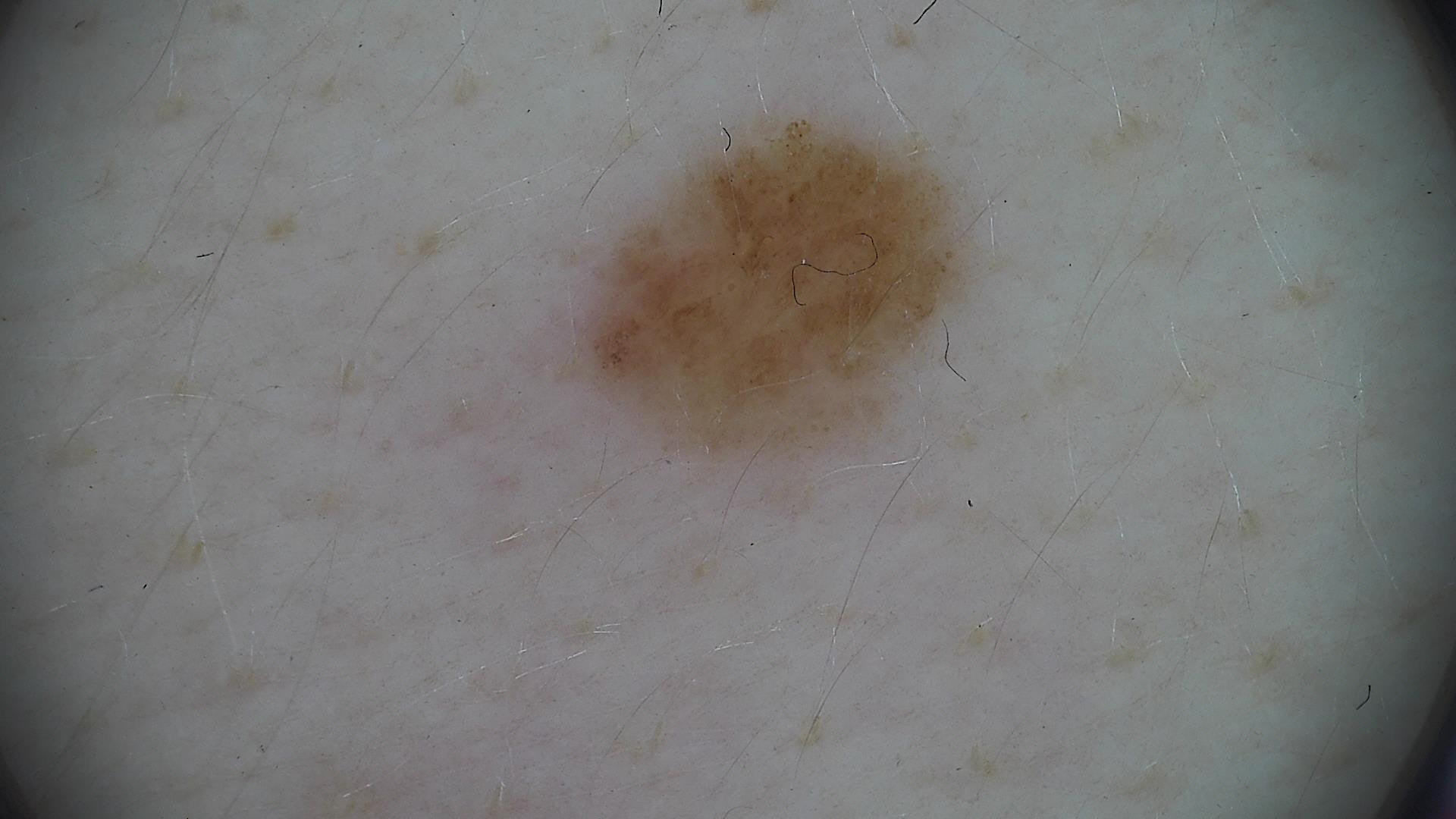A dermoscopic photograph of a skin lesion. Classified as a benign lesion — a dysplastic junctional nevus.